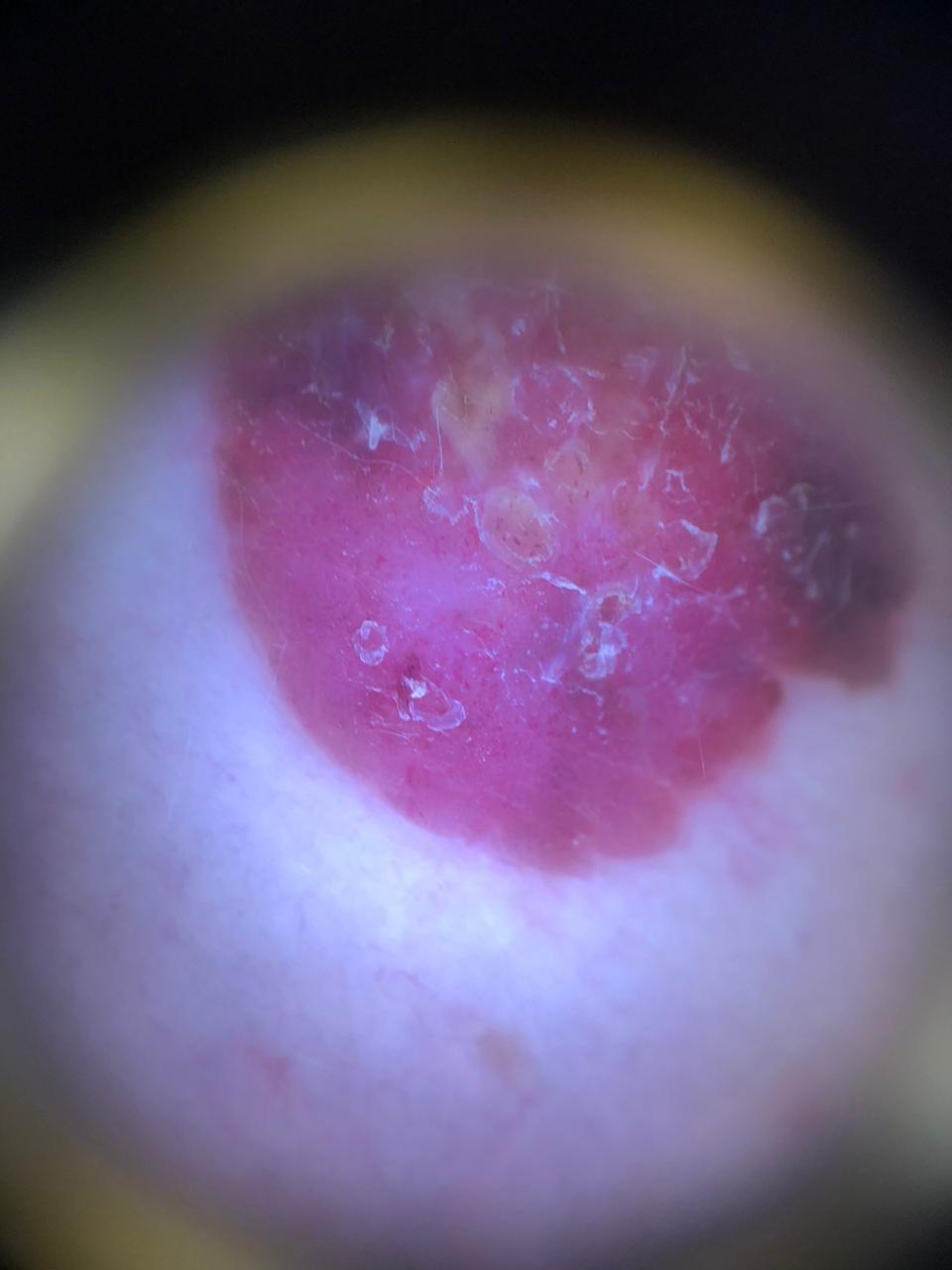{"lesion_location": {"region": "a lower extremity"}, "diagnosis": {"name": "Melanoma", "malignancy": "malignant", "confirmation": "histopathology"}}